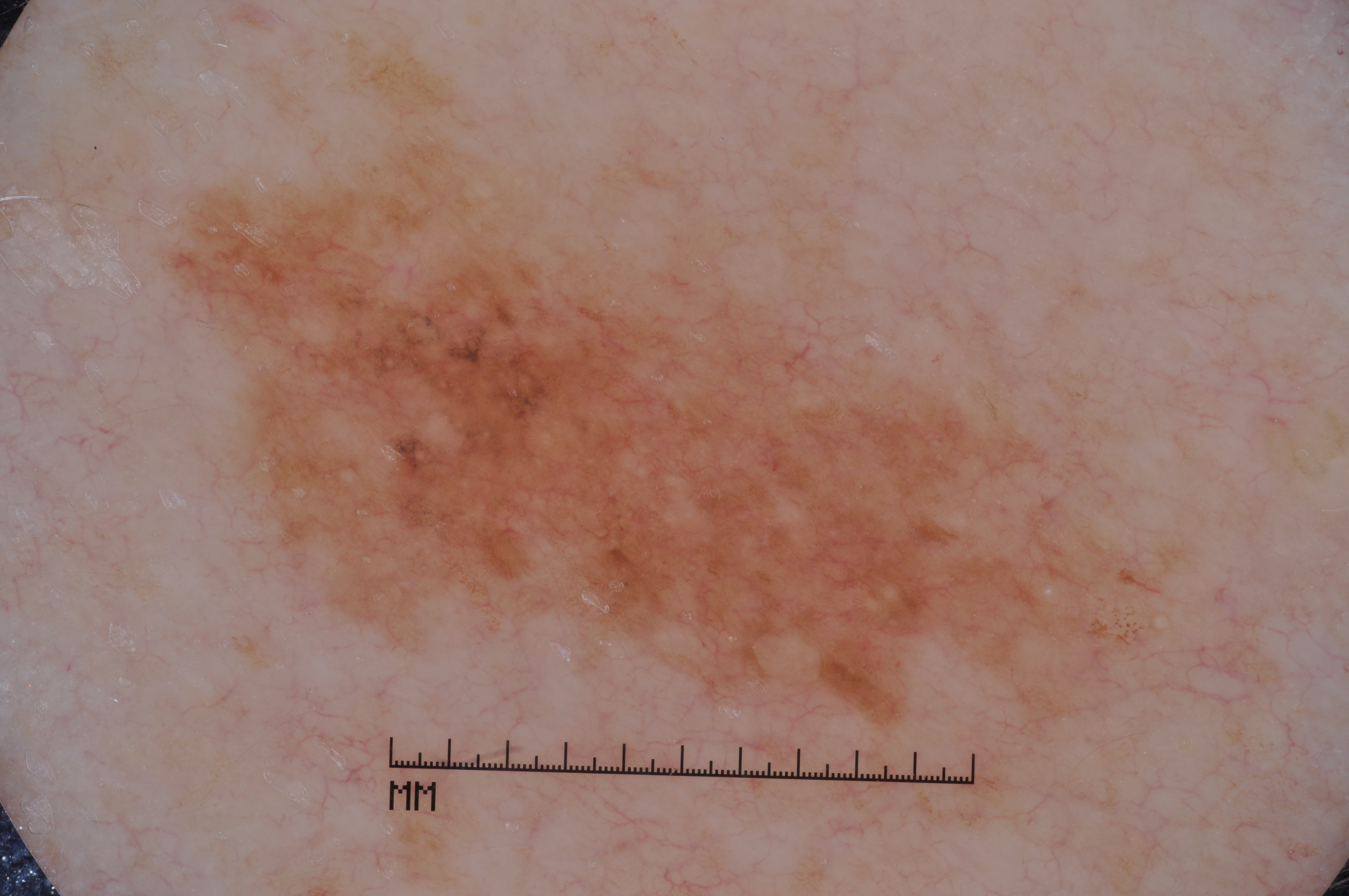Image and clinical context: A dermoscopy image of a single skin lesion. A male subject, aged approximately 65. The lesion takes up a moderate portion of the field. Dermoscopic examination shows milia-like cysts and pigment network, with no negative network or streaks. In (x1, y1, x2, y2) order, the visible lesion spans box(159, 36, 1192, 778). Diagnosis: Biopsy-confirmed as a melanoma, a malignant lesion.